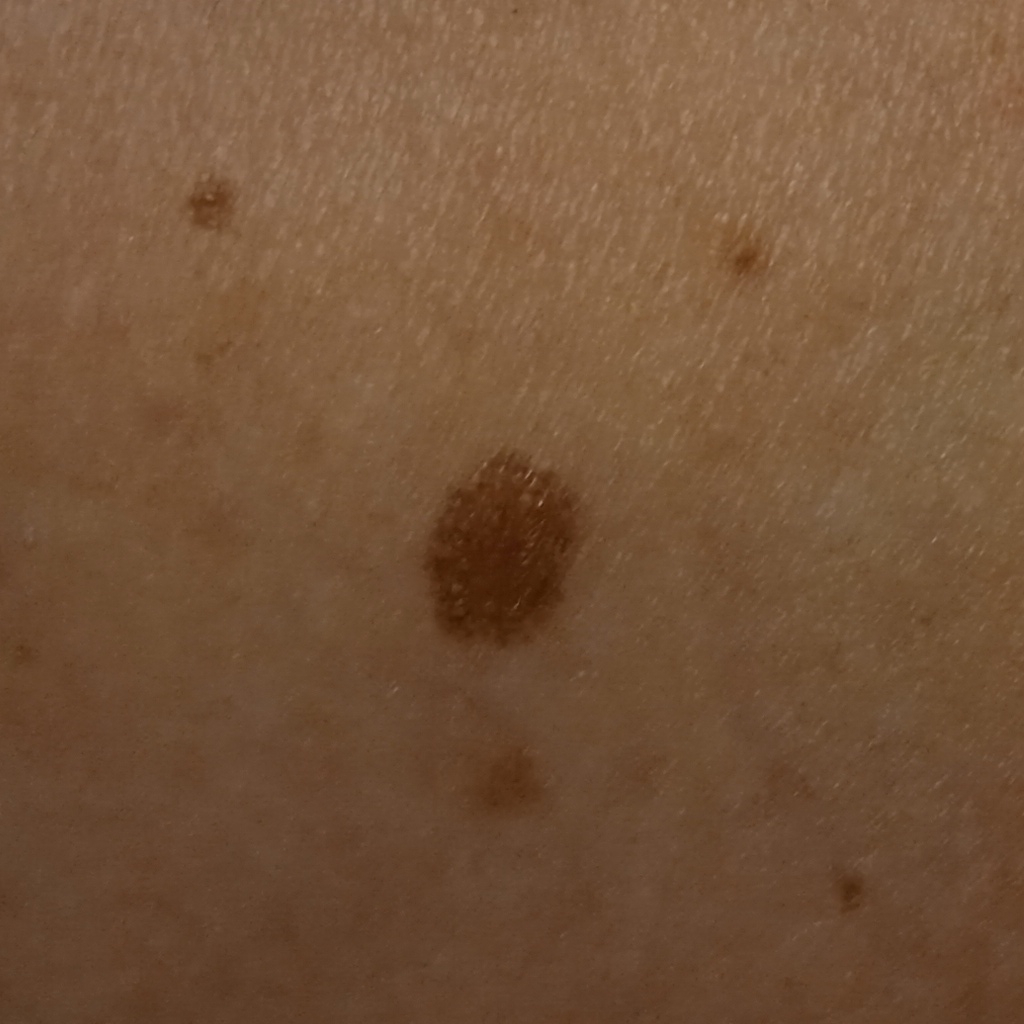patient: female, aged 59 | image type: clinical photograph | nevus count: a moderate number of melanocytic nevi | body site: an arm | lesion size: 6.7 mm | pathology: atypical (dysplastic) nevus — biopsy-proven.